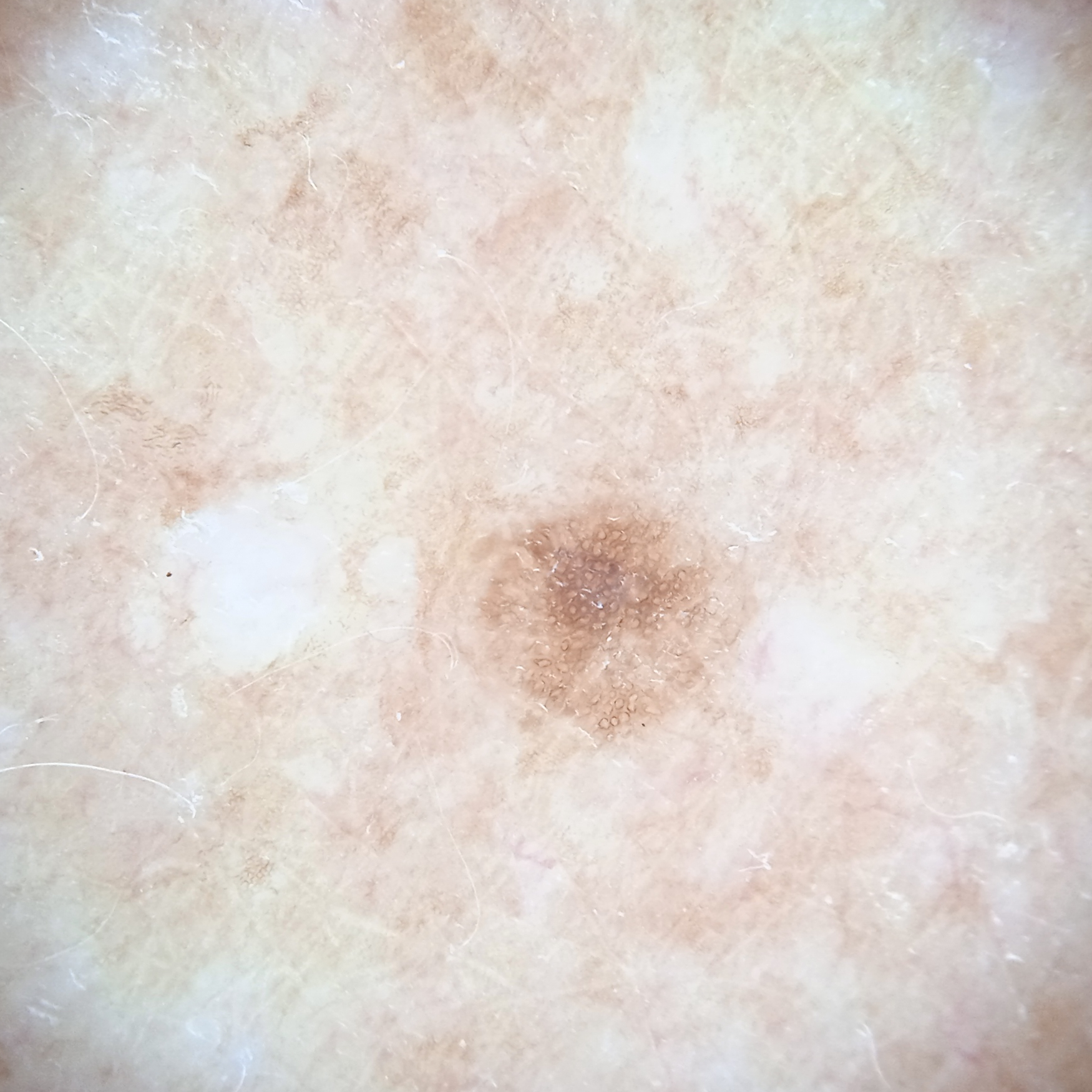  risk_factors:
    positive:
      - a personal history of skin cancer
      - a personal history of cancer
    negative:
      - no prior organ transplant
  referral: research study (no referral diagnosis)
  mole_burden: a moderate number of melanocytic nevi
  patient:
    age: 75
    sex: female
  lesion_location: the back
  diagnosis:
    name: melanocytic nevus
    malignancy: benign